The patient is a male roughly 65 years of age. A dermoscopy image of a single skin lesion.
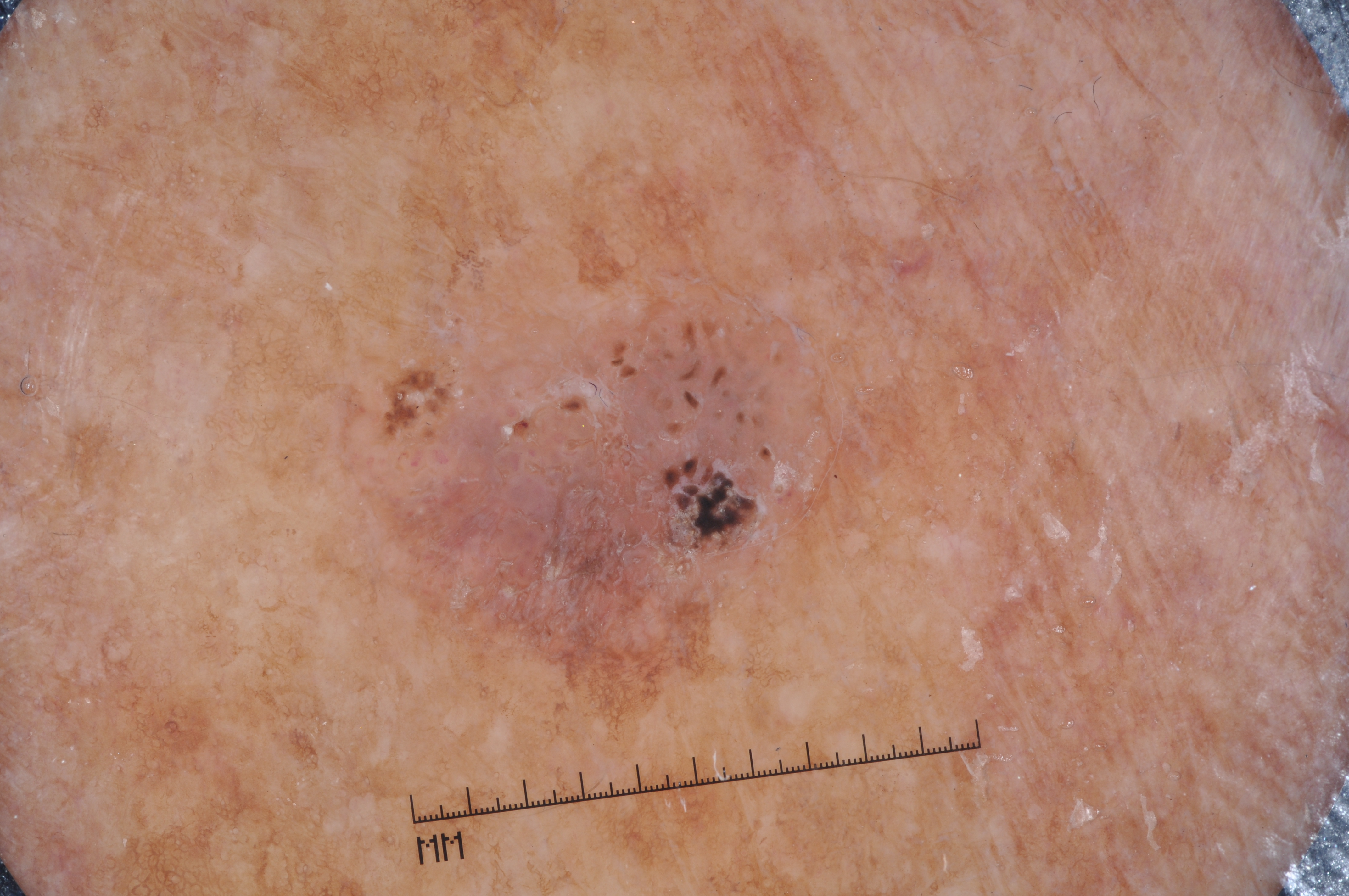Case summary: The visible lesion spans 347, 301, 834, 727. Dermoscopic examination shows milia-like cysts; no pigment network, negative network, or streaks. A mid-sized lesion within the field. Conclusion: The diagnostic assessment was a seborrheic keratosis.